Acquired for a research image collection, with no referral diagnosis; a dermatoscopic image of a skin lesion; on a questionnaire the patient reported immunosuppression, a prior organ transplant, and no personal history of cancer; the patient says their skin reddens painfully with sun exposure; a moderate number of moles by the patient's own estimate — 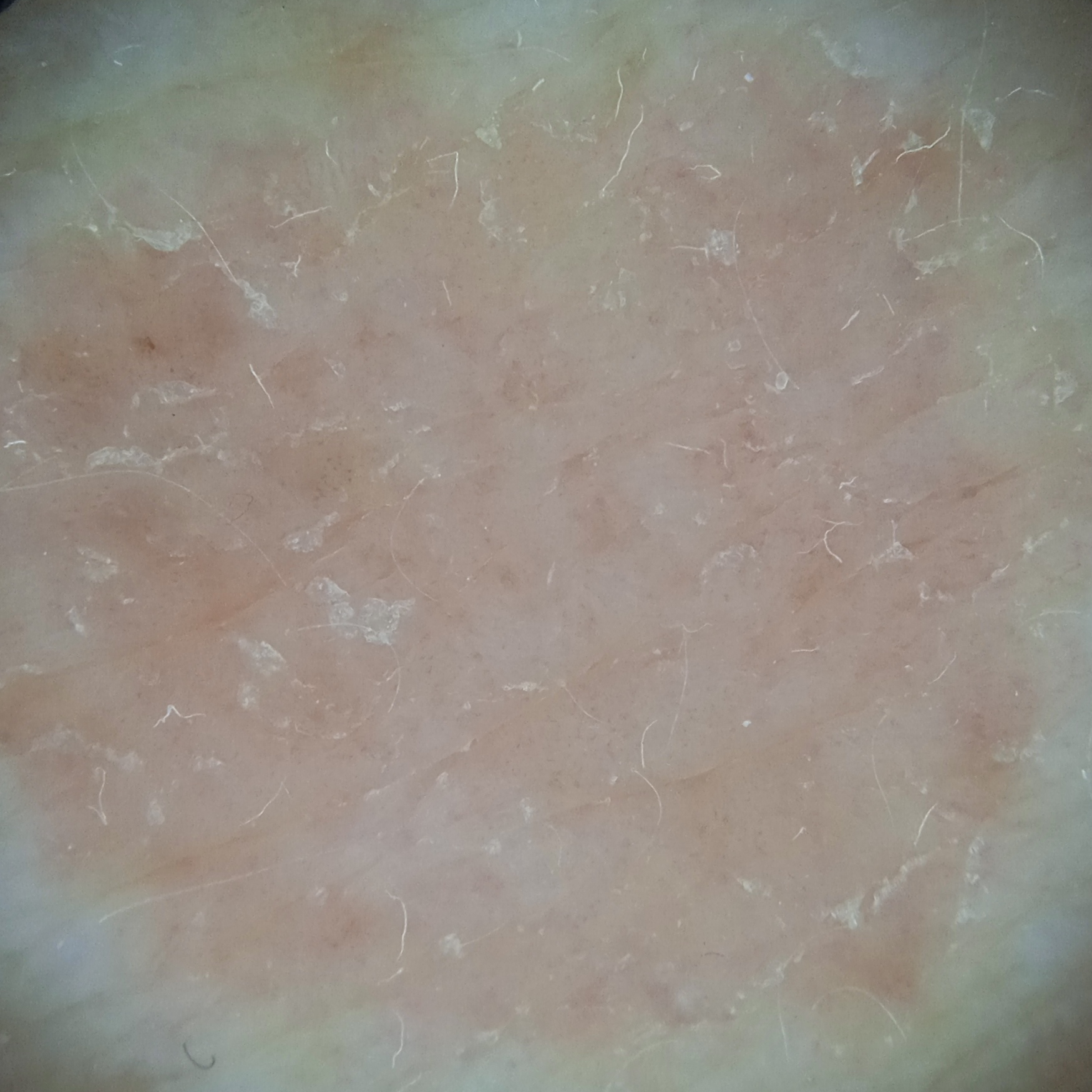Case:
* location: an arm
* size: 13.2 mm
* diagnostic label: basal cell carcinoma (dermatologist consensus)